A clinical photo of a skin lesion taken with a smartphone: 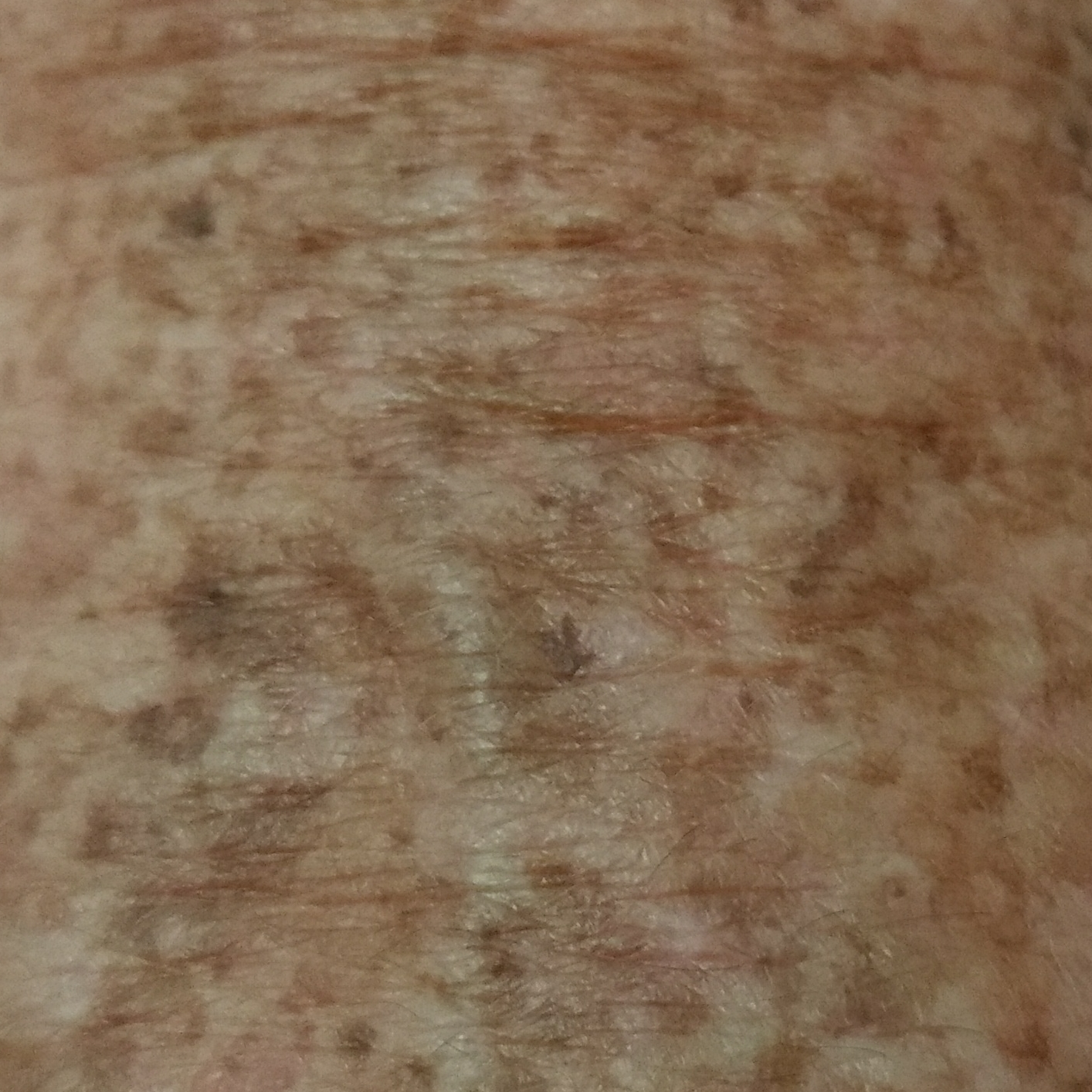Located on a forearm. Diagnosed by dermatologist consensus as a seborrheic keratosis.